Texture is reported as flat. The lesion is associated with itching. Skin tone: Fitzpatrick phototype IV. This is a close-up image. Present for less than one week: 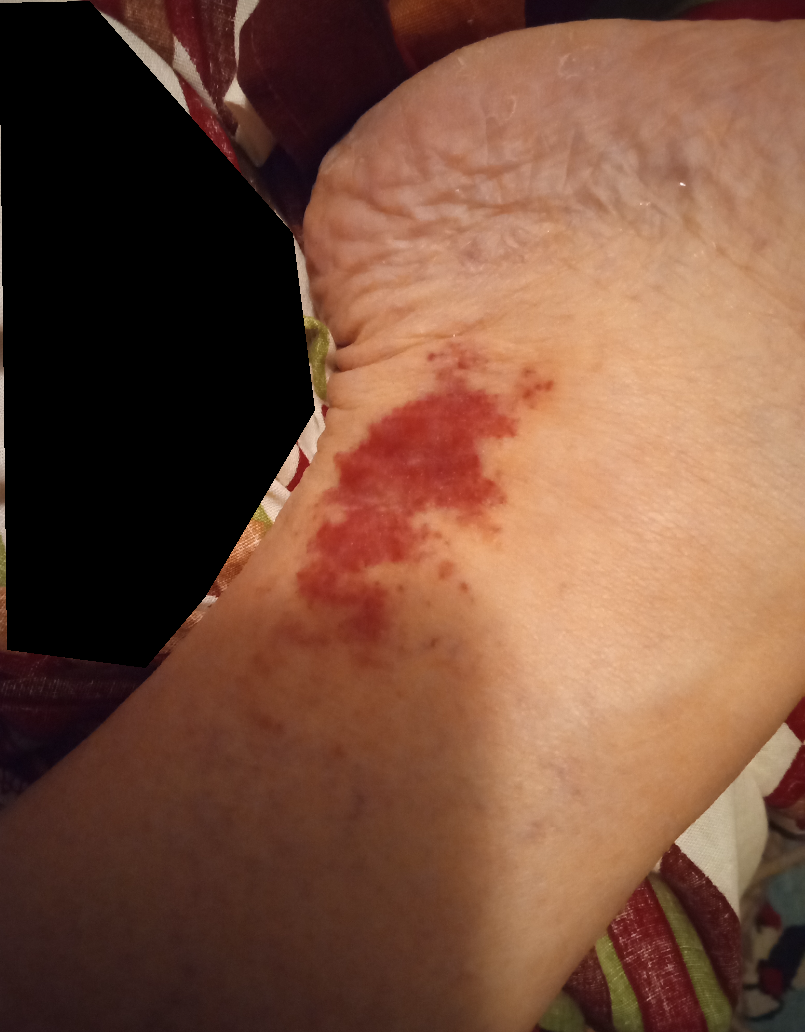<dermatology_case>
  <differential>
    <Pigmented purpuric eruption>0.41</Pigmented purpuric eruption>
    <ecchymoses>0.41</ecchymoses>
    <Kaposi's sarcoma of skin>0.18</Kaposi's sarcoma of skin>
  </differential>
</dermatology_case>